A dermoscopic image of a skin lesion.
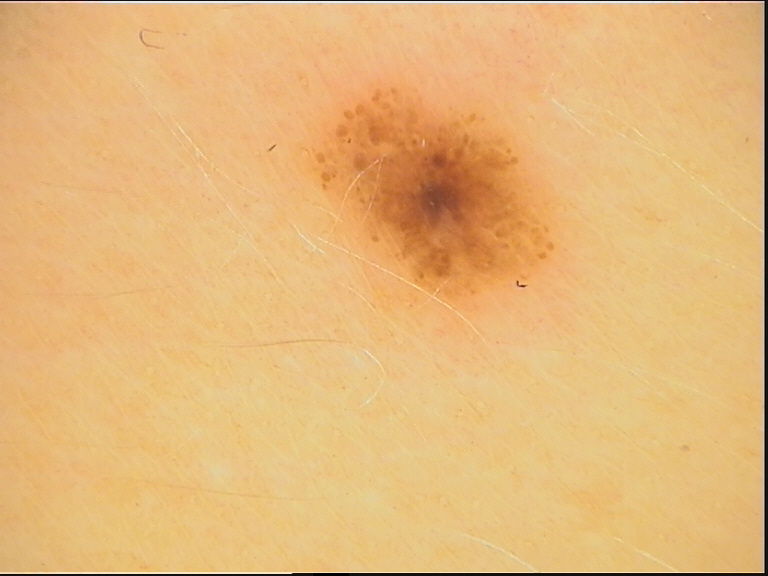diagnosis — dysplastic compound nevus (expert consensus)